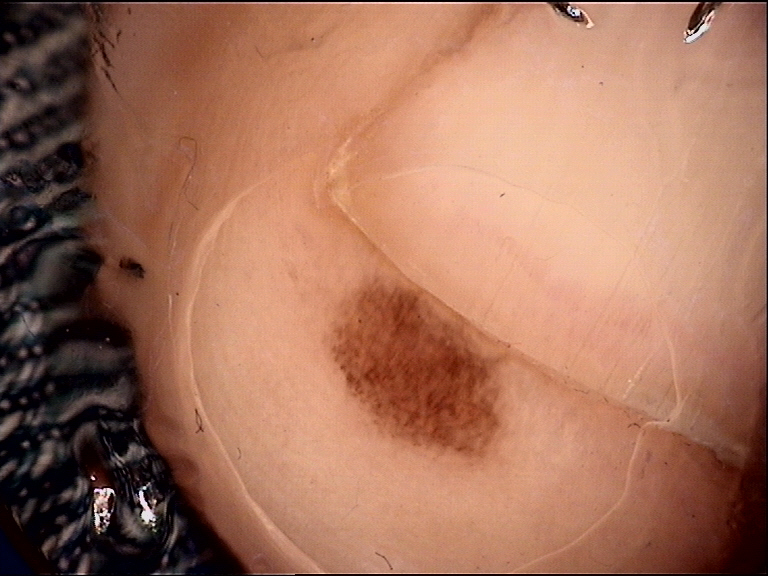A dermoscopic image of a skin lesion.
The architecture is that of a banal lesion.
Labeled as an acral junctional nevus.